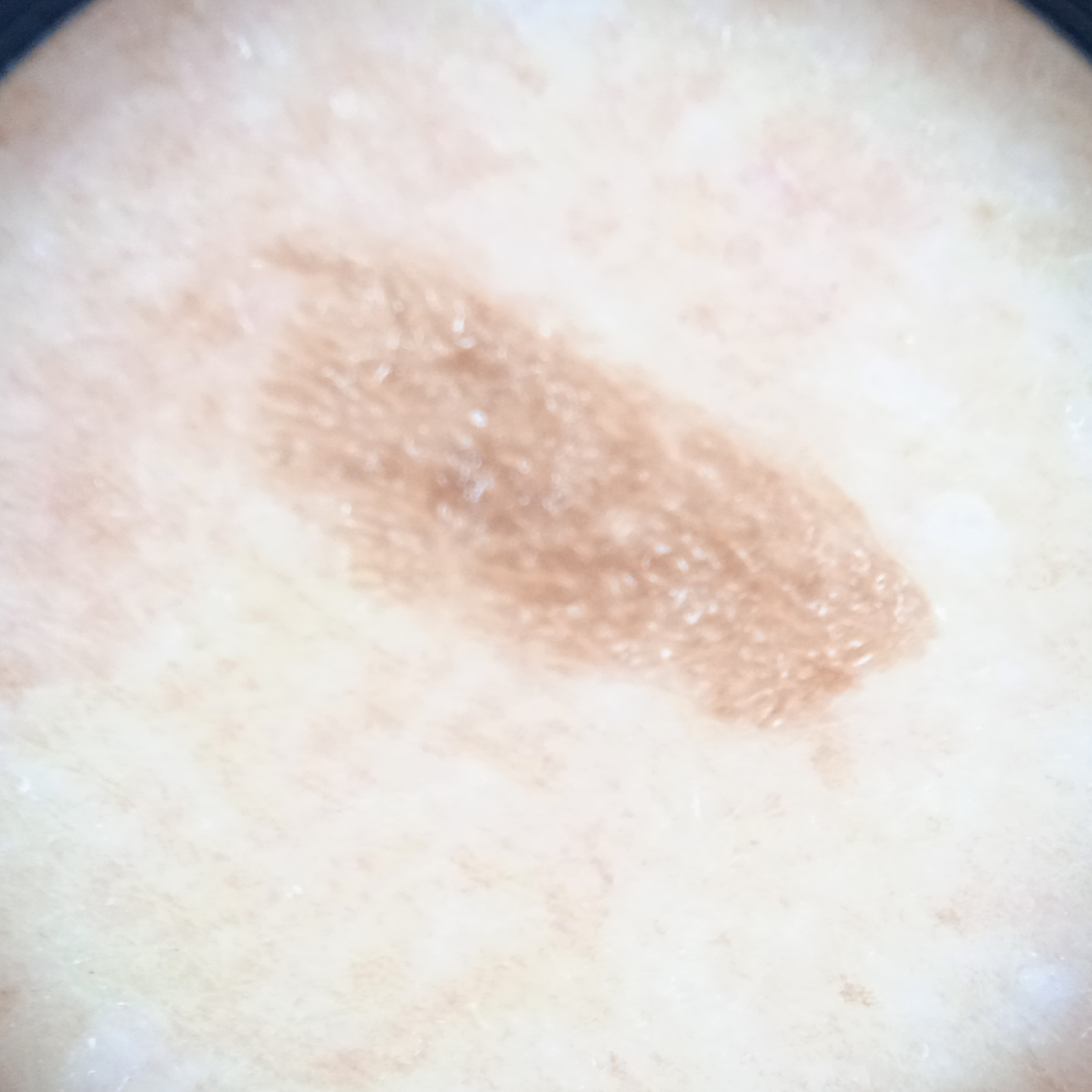A female subject age 75.
Collected as part of a research study, without a referral diagnosis.
A skin lesion imaged with a dermatoscope.
The lesion is on the back.
The lesion measures approximately 8.4 mm.
The consensus diagnosis for this lesion was a seborrheic keratosis.